A dermoscopic image of a skin lesion:
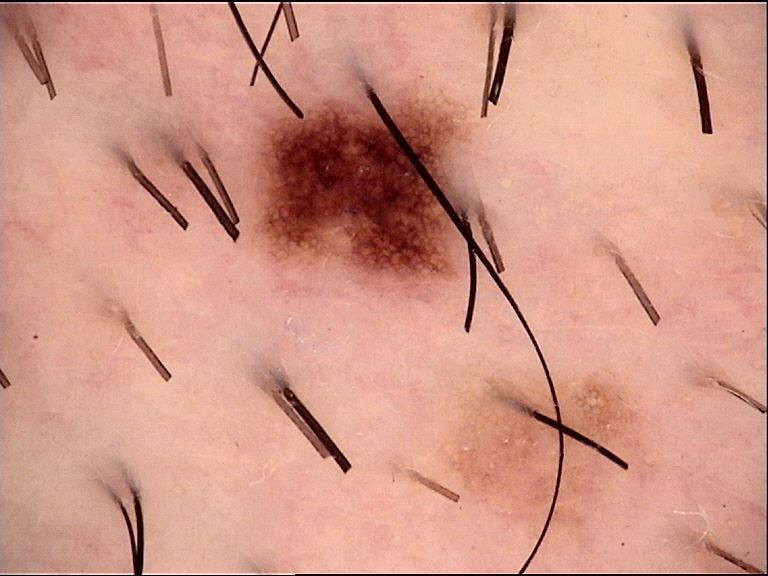Classified as a benign lesion — a dysplastic junctional nevus.